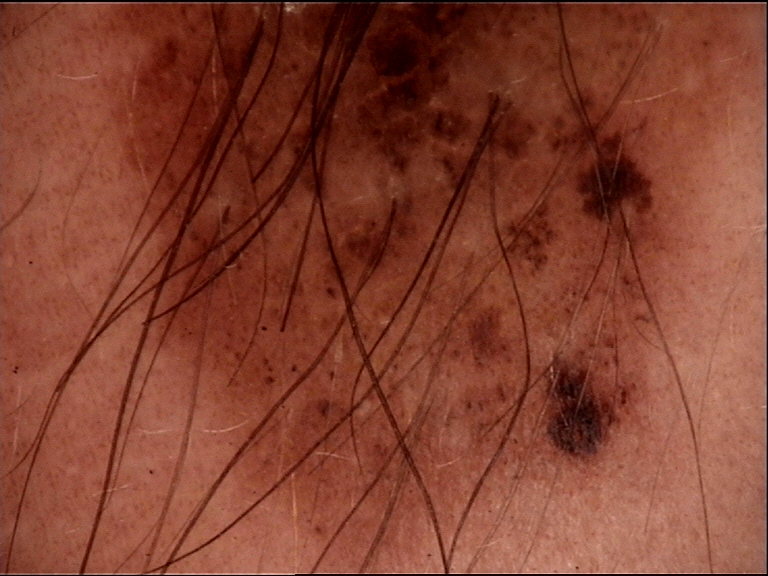A skin lesion imaged with a dermatoscope. The diagnosis was a banal lesion — a congenital compound nevus.